The chart records no previous melanoma and no melanoma in first-degree relatives · a male subject in their 80s · a dermoscopy image of a single skin lesion · skin type II: 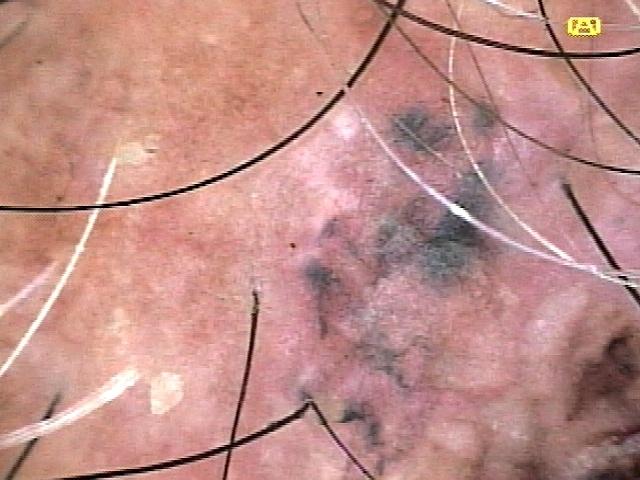Image and clinical context: Located on the head or neck. Diagnosis: Histopathological examination showed a malignant, adnexal lesion — a basal cell carcinoma.